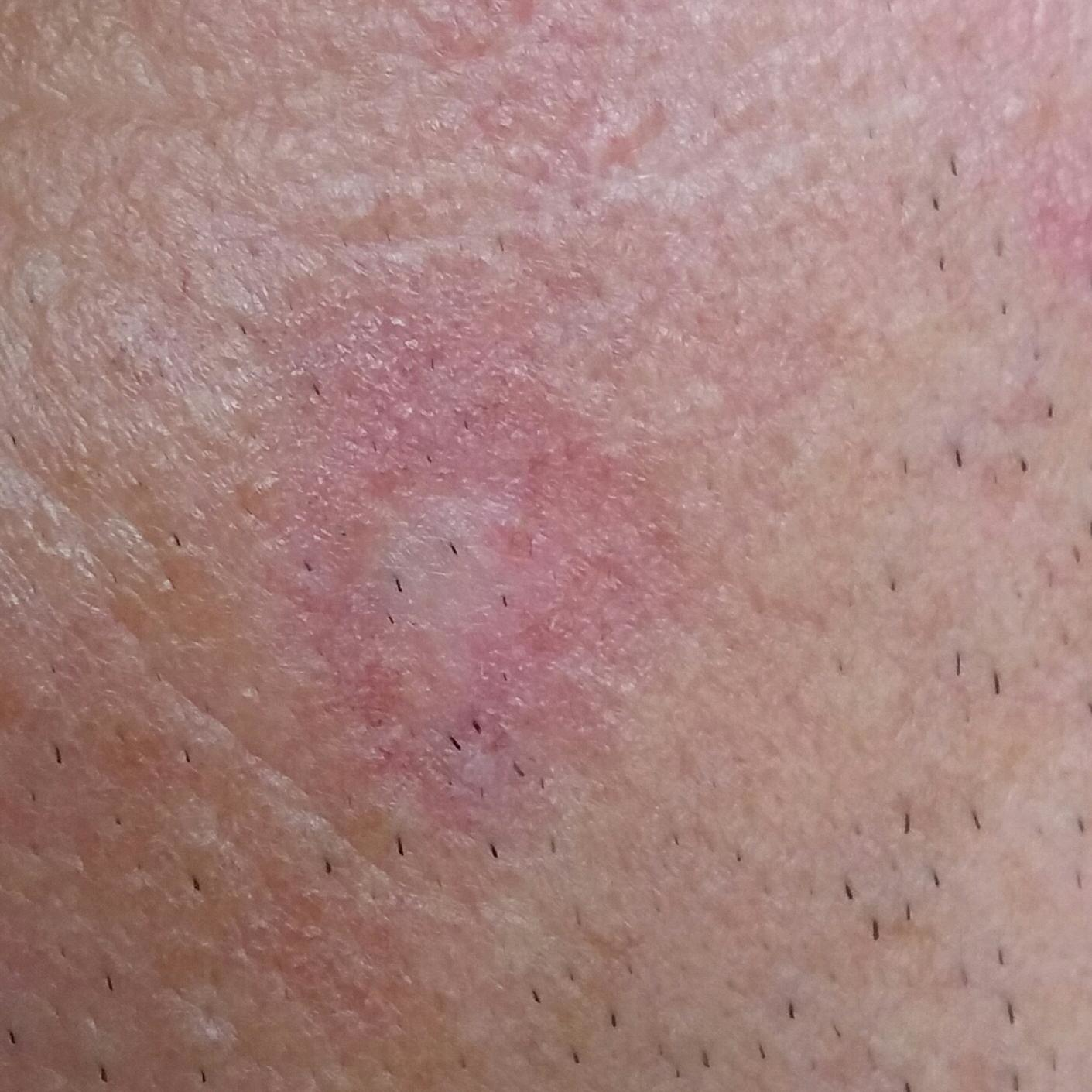A smartphone photograph of a skin lesion.
The lesion was found on the face.
Per patient report, the lesion itches, but has not bled.
The consensus clinical diagnosis was an actinic keratosis.